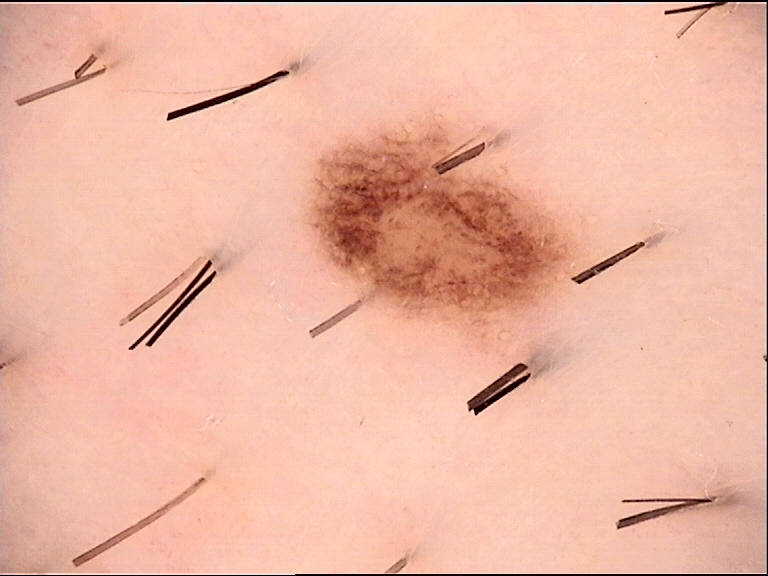Case:
- diagnosis · dysplastic junctional nevus (expert consensus)